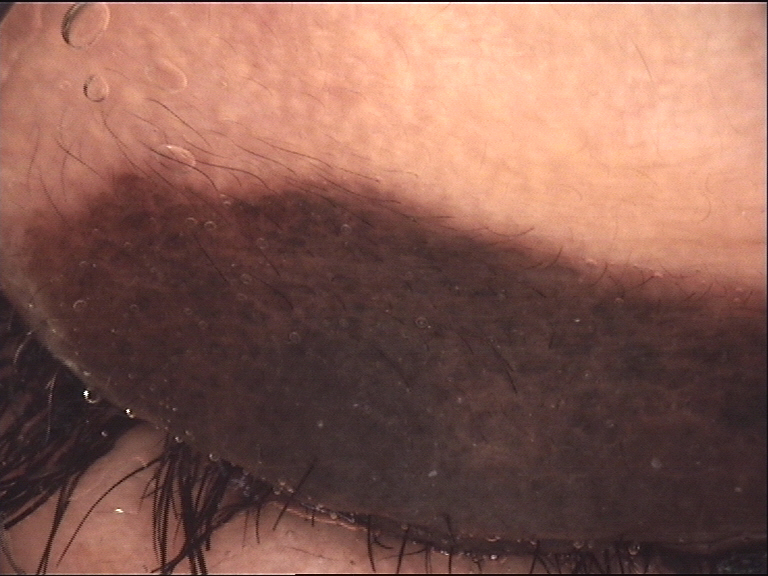Conclusion: The diagnosis was a congenital compound nevus.